Fitzpatrick V; non-clinician graders estimated Monk Skin Tone 4 or 7 (two reviewer pools disagreed). Symptoms reported: bothersome appearance, itching and enlargement. The photograph is a close-up of the affected area. The lesion is described as rough or flaky and flat. The patient described the issue as a rash. The head or neck is involved.
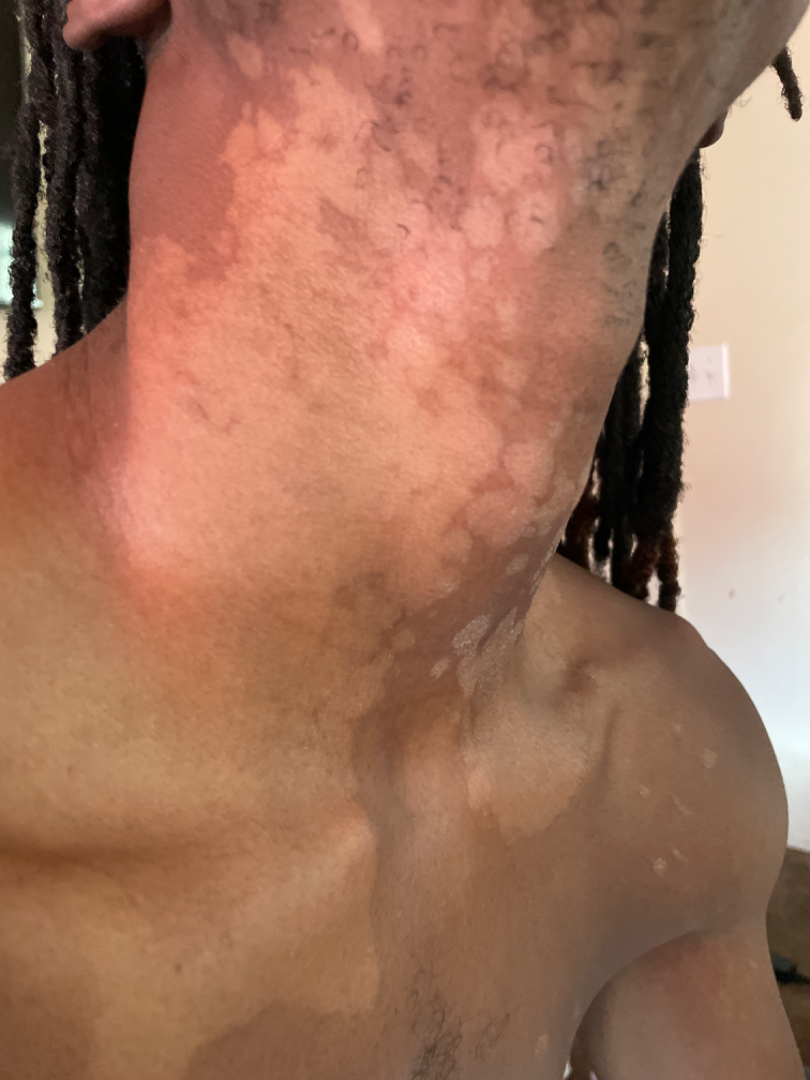| key | value |
|---|---|
| assessment | indeterminate |